A skin lesion imaged with a dermatoscope.
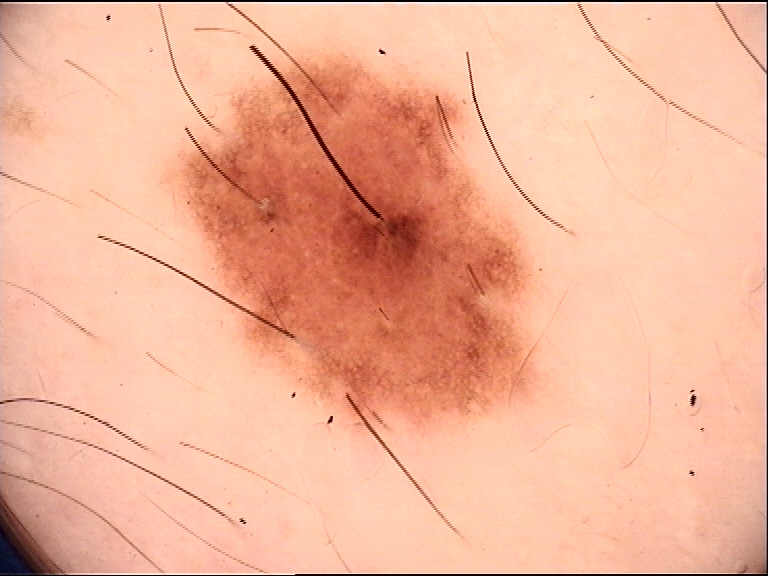| field | value |
|---|---|
| label | dysplastic compound nevus (expert consensus) |